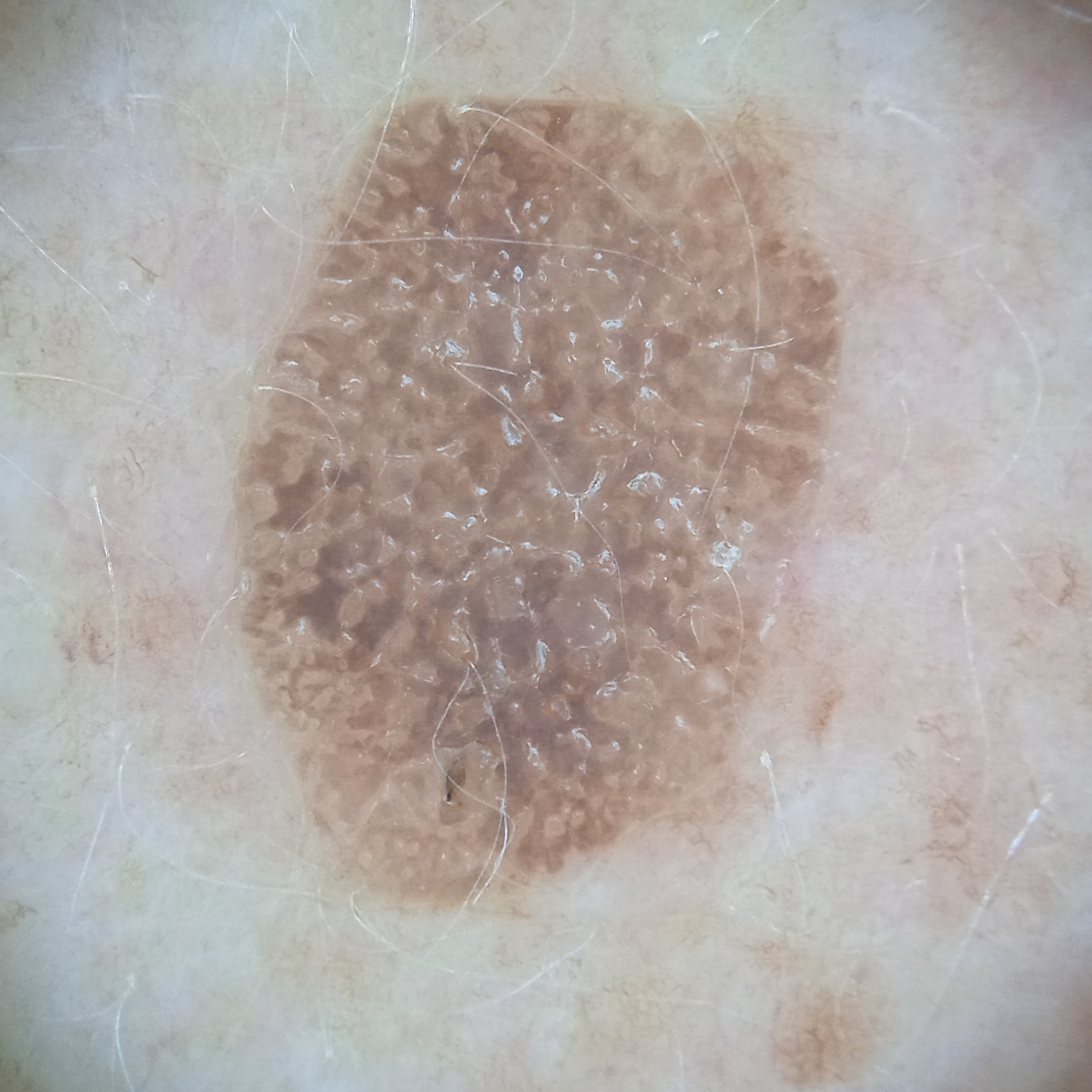- sun reaction — skin tans without first burning
- image — dermatoscopic image
- nevus count — numerous melanocytic nevi
- patient — female, 78 years old
- clinical context — research study (no referral diagnosis)
- site — the back
- assessment — seborrheic keratosis (dermatologist consensus)